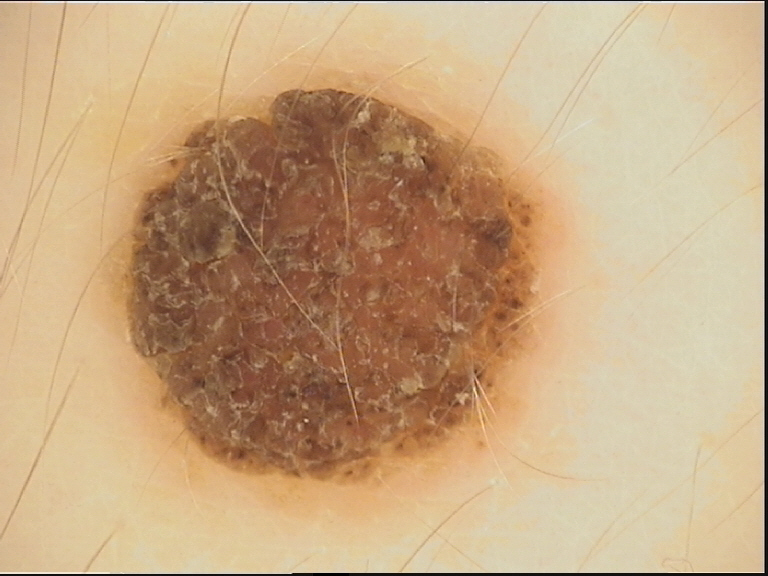Classified as a banal lesion — a compound nevus.